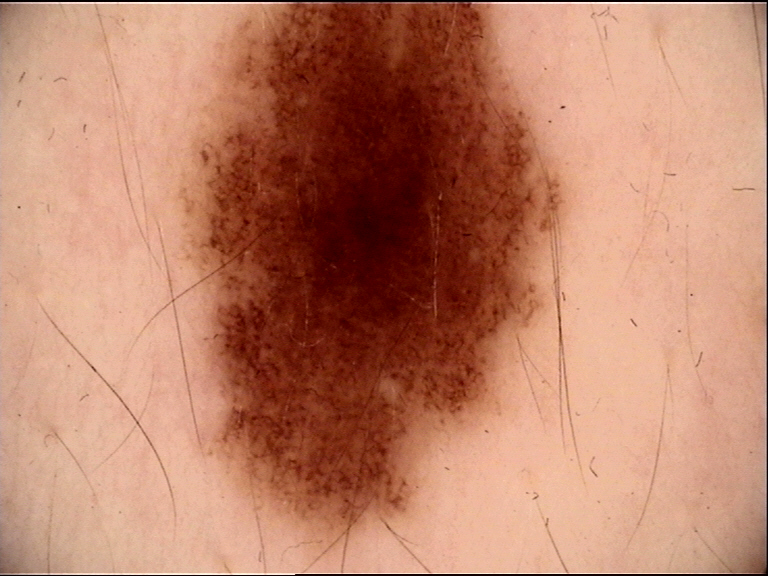A dermoscopy image of a single skin lesion. Diagnosed as a dysplastic junctional nevus.